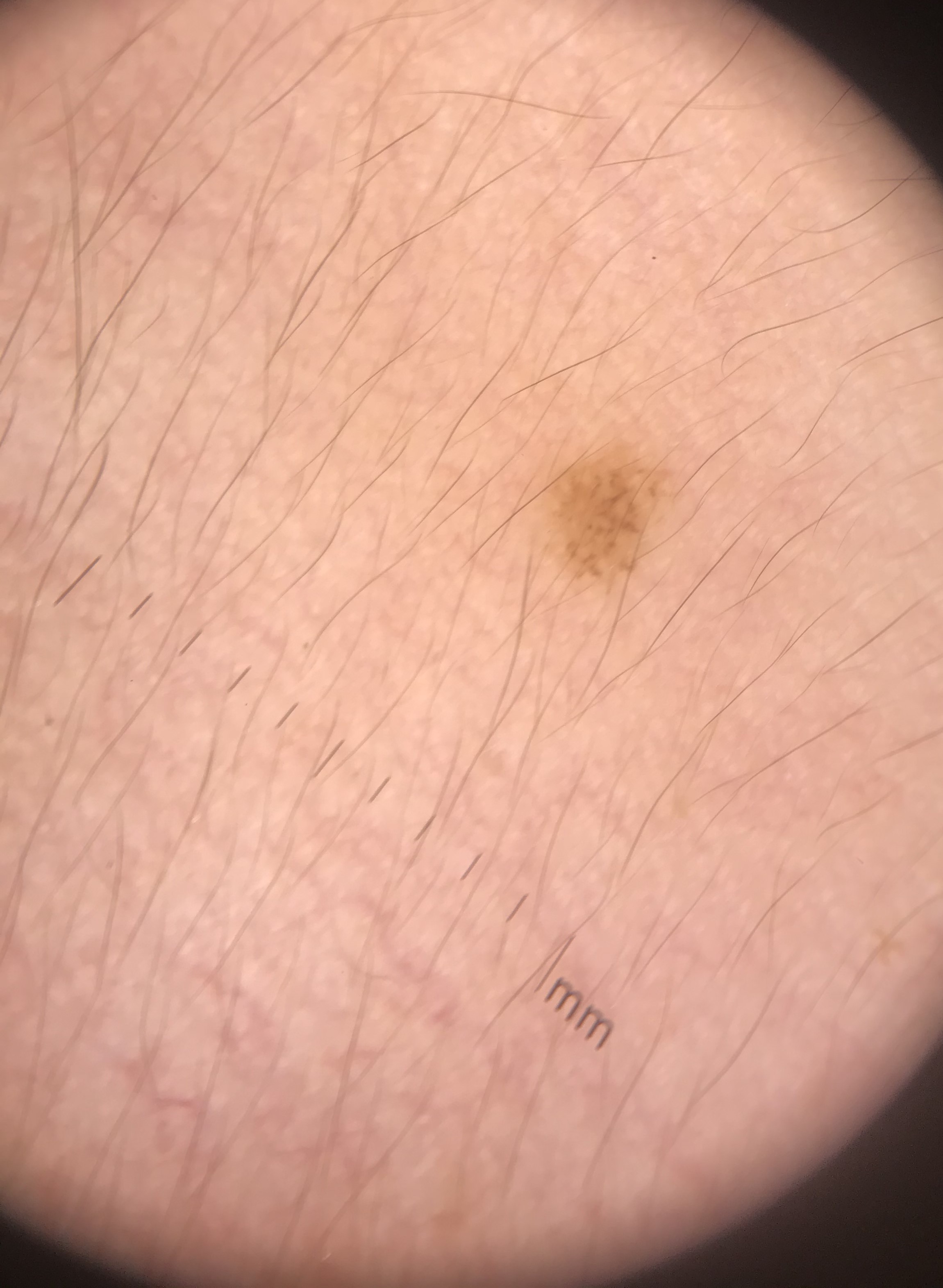A dermoscopic photograph of a skin lesion.
The architecture is that of a compound, banal lesion.
The diagnostic label was a Miescher nevus.